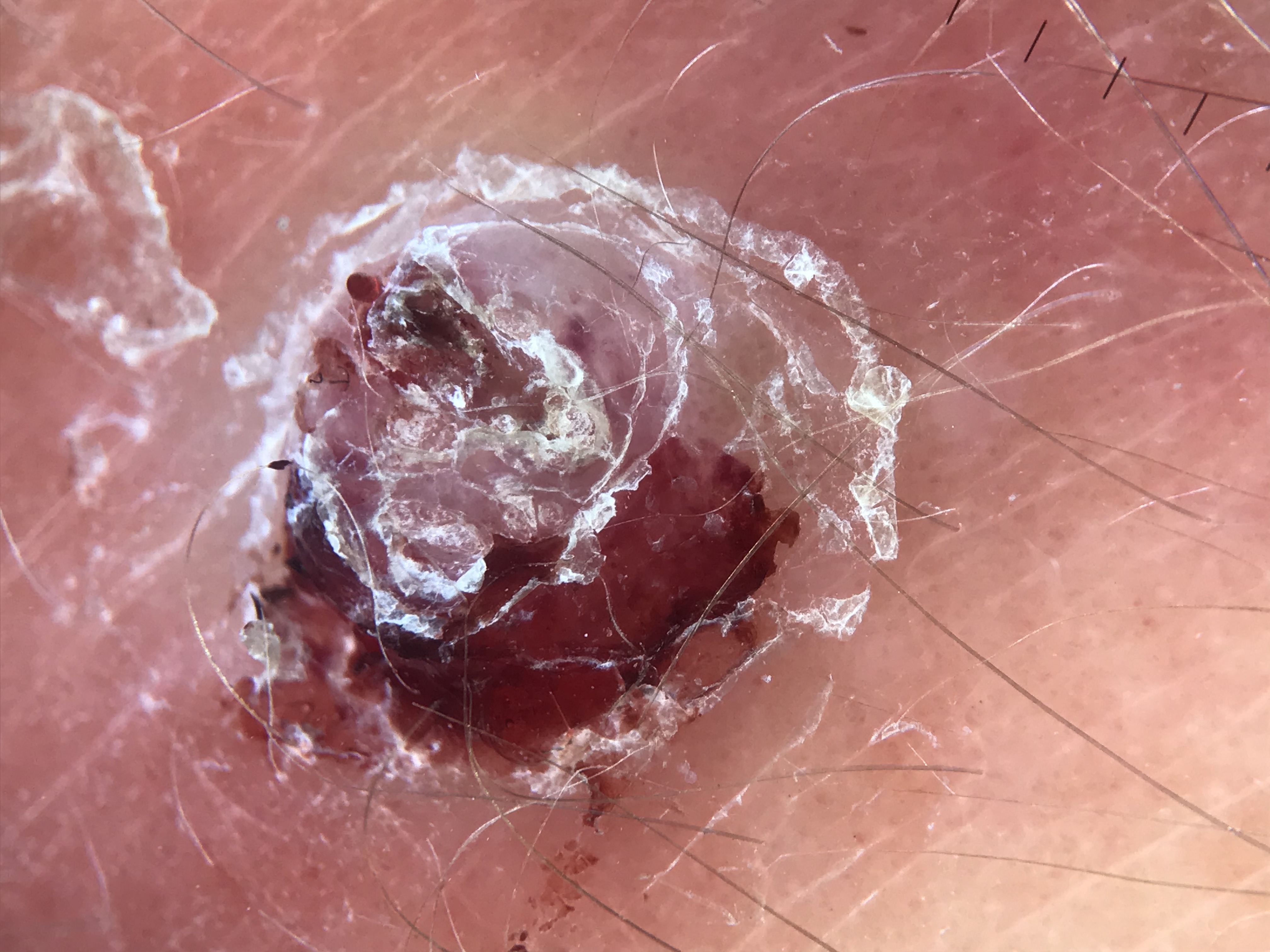class: squamous cell carcinoma (biopsy-proven)